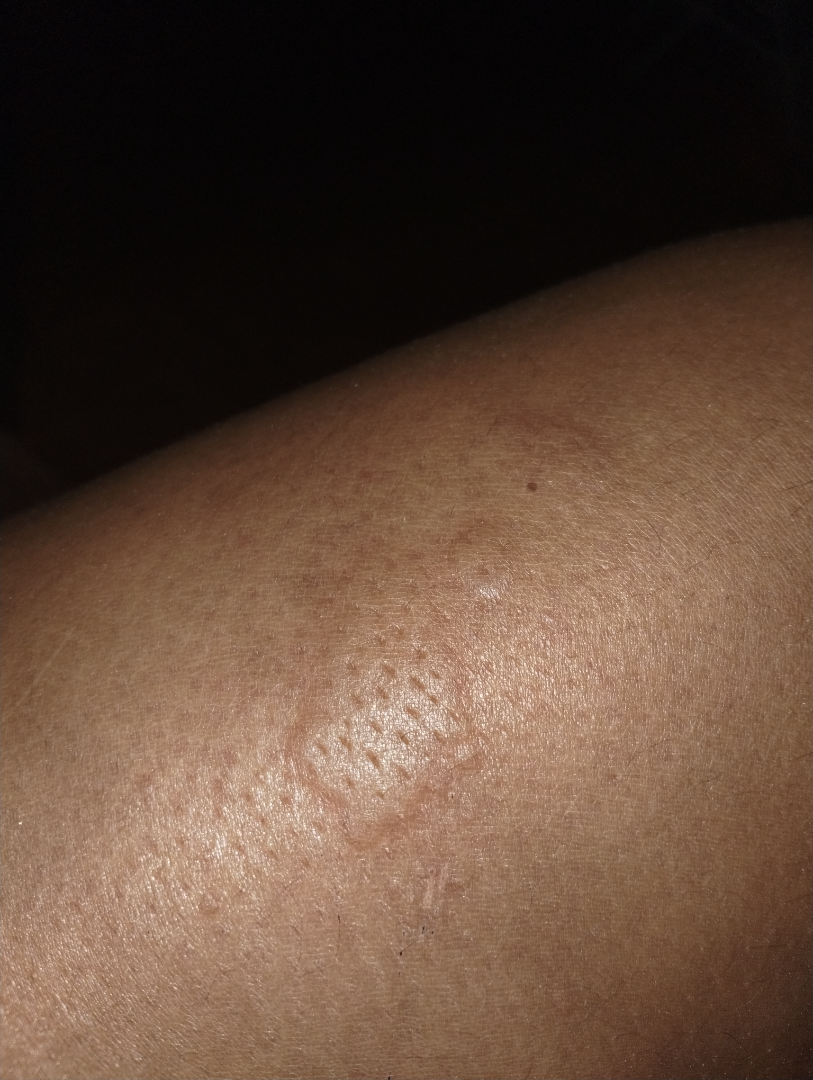Skin tone: Fitzpatrick IV. The patient reported no relevant symptoms from the lesion. The subject is female. The patient described the issue as skin that appeared healthy to them. The lesion involves the arm and leg. The photograph is a close-up of the affected area. Single-reviewer assessment: the leading impression is Urticaria; the differential also includes Hypersensitivity; less probable is Insect Bite.